Close-up view — 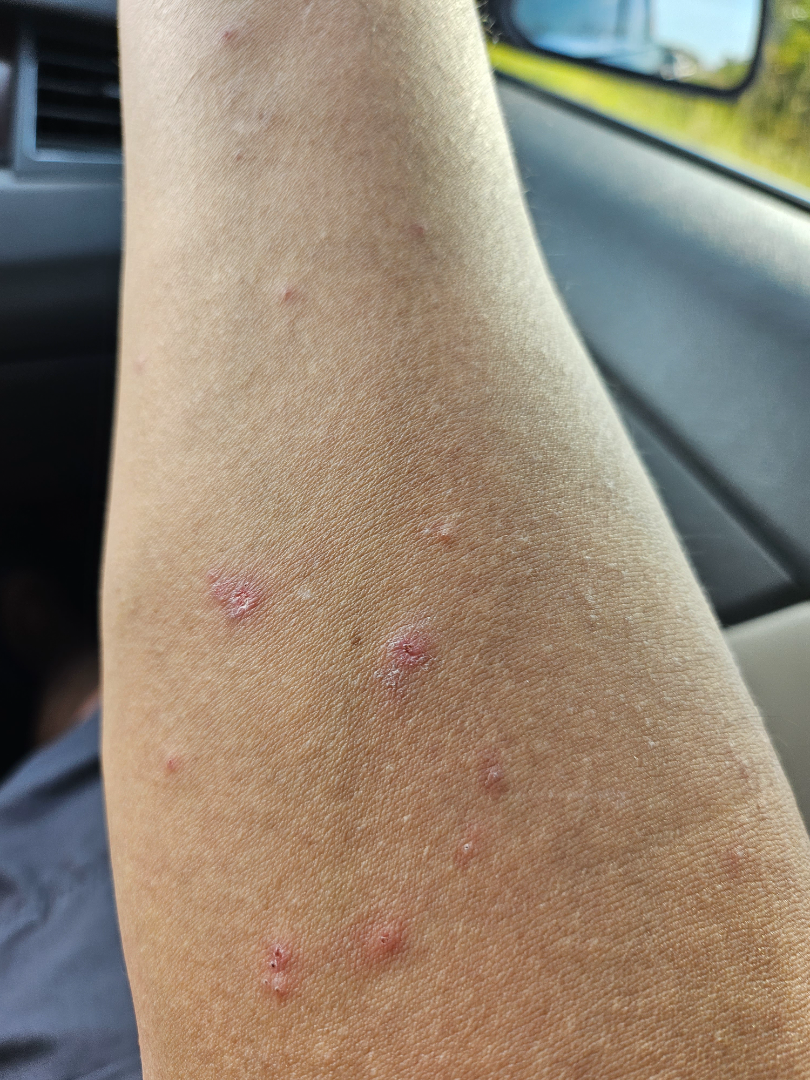Most likely Lichen planus/lichenoid eruption; with consideration of Eczema; also on the differential is Insect Bite.